The photograph is a close-up of the affected area: 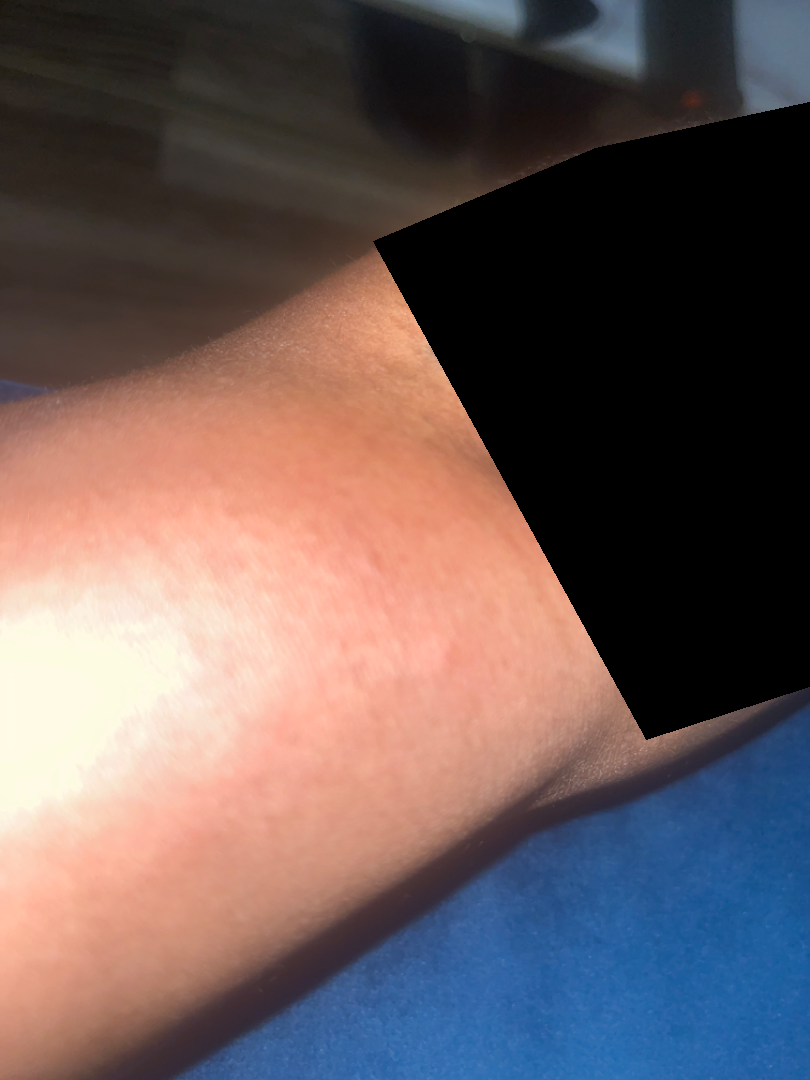– assessment · could not be assessed